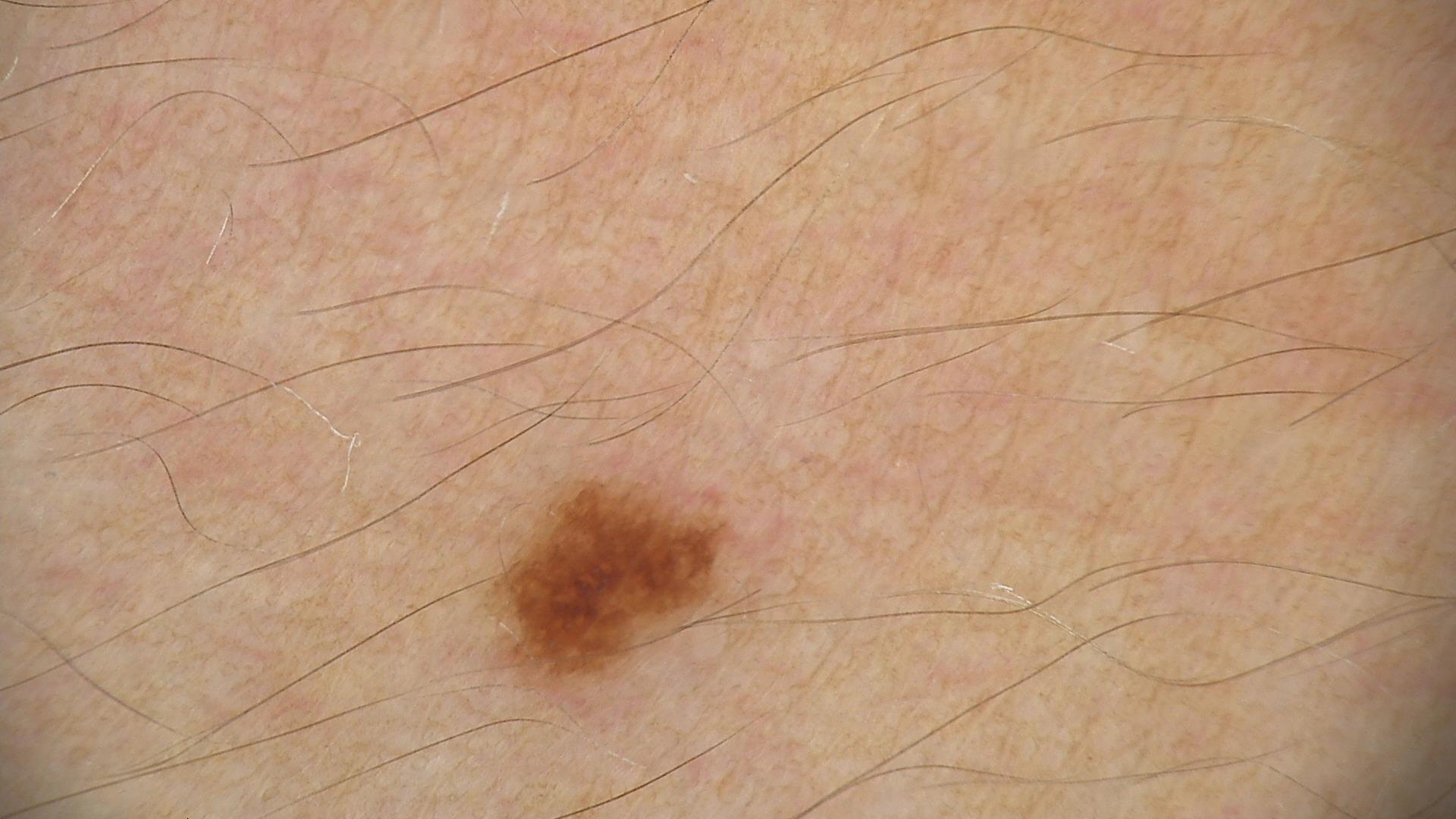A dermoscopic image of a skin lesion. The diagnostic label was a benign lesion — a dysplastic junctional nevus.